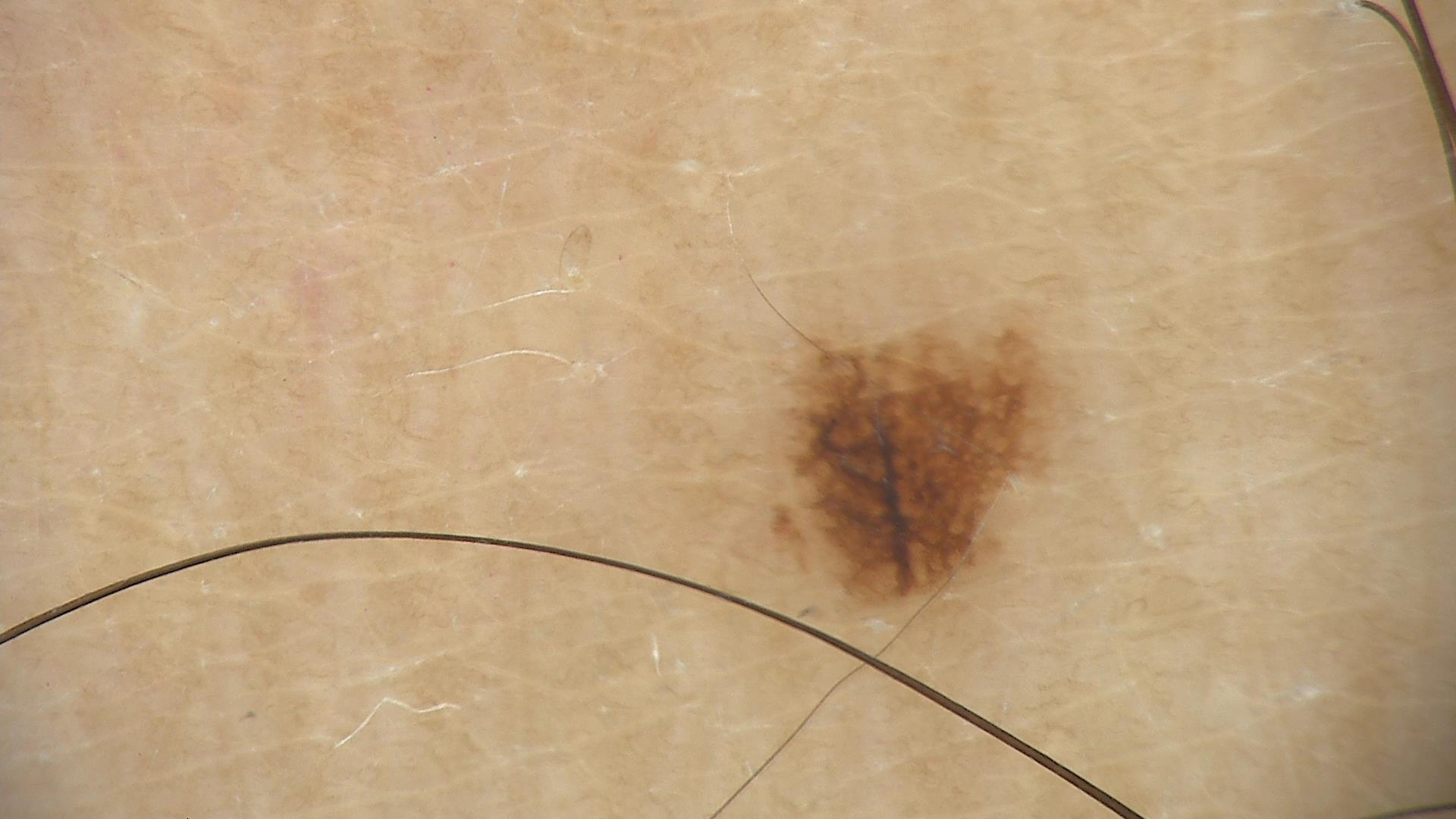The diagnosis was a dysplastic junctional nevus.